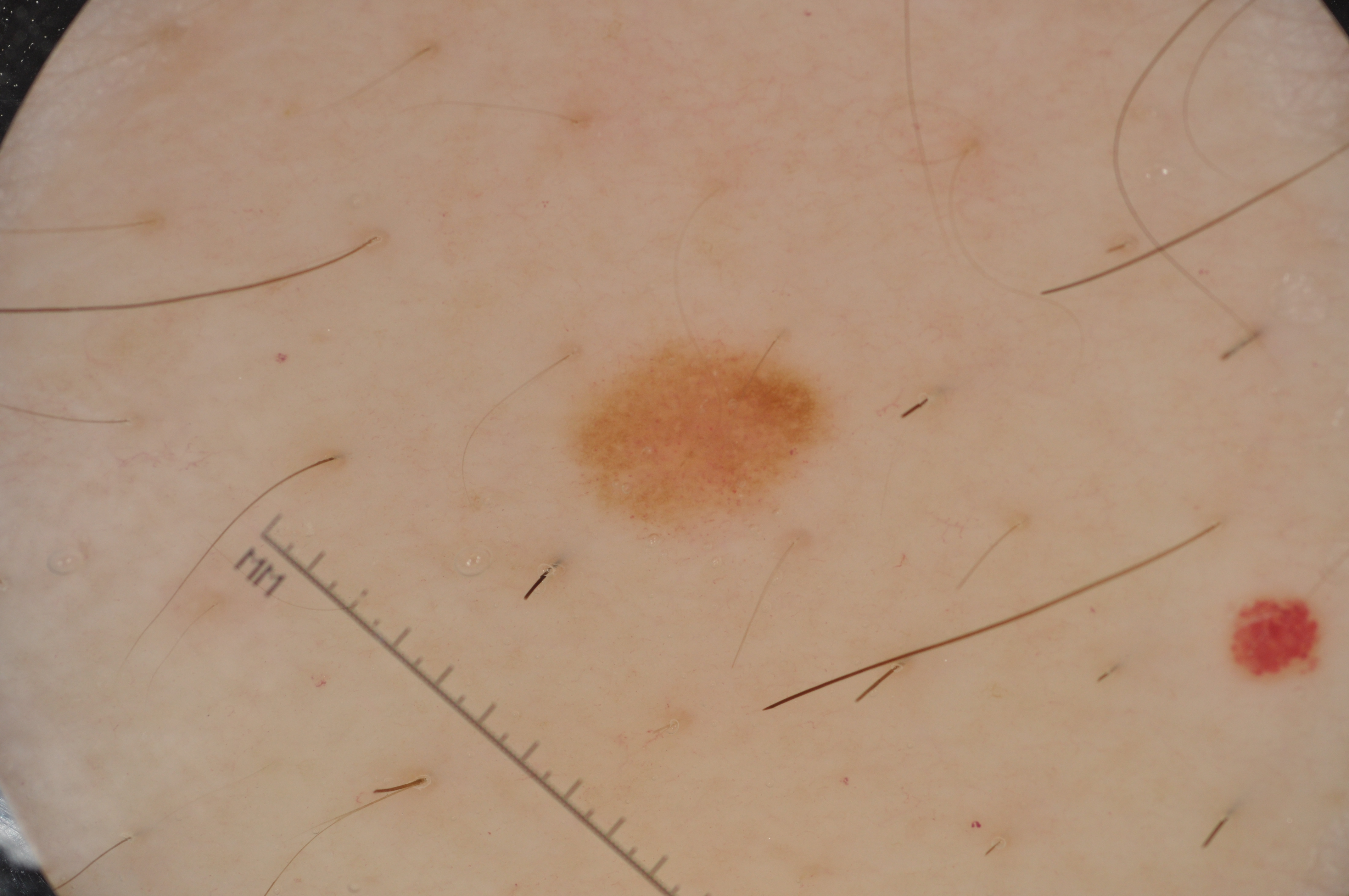<dermoscopy>
  <patient>
    <sex>male</sex>
    <age_approx>55</age_approx>
  </patient>
  <image>
    <modality>dermoscopy</modality>
  </image>
  <lesion_extent>
    <approx_field_fraction_pct>3</approx_field_fraction_pct>
  </lesion_extent>
  <dermoscopic_features>
    <present>milia-like cysts, pigment network</present>
    <absent>streaks, negative network</absent>
  </dermoscopic_features>
  <lesion_location>
    <bbox_xyxy>569, 343, 822, 525</bbox_xyxy>
  </lesion_location>
  <diagnosis>
    <name>melanocytic nevus</name>
    <malignancy>benign</malignancy>
    <lineage>melanocytic</lineage>
    <provenance>clinical</provenance>
  </diagnosis>
</dermoscopy>